A male patient approximately 50 years of age. A dermoscopic close-up of a skin lesion.
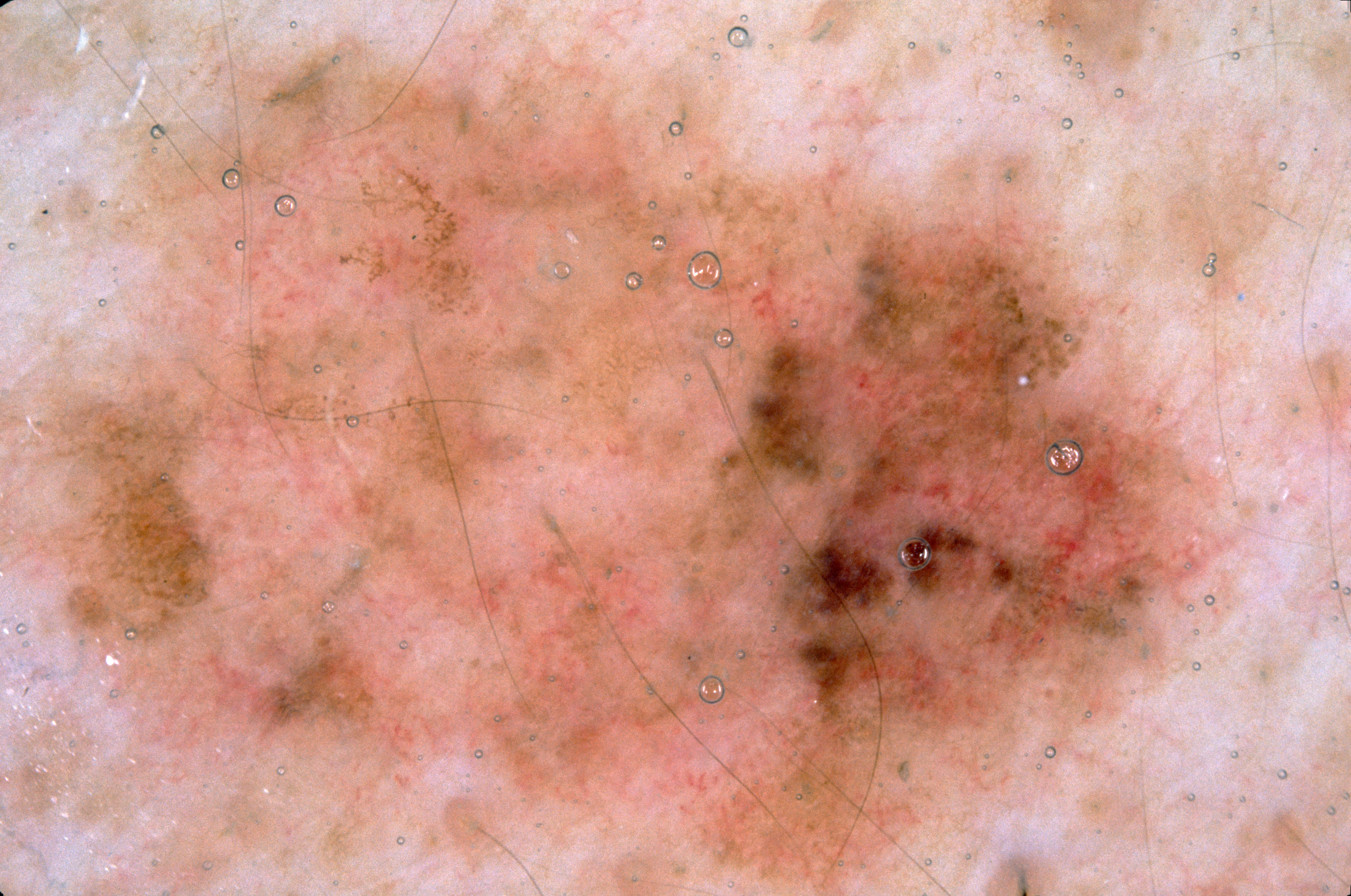Q: Which assessed dermoscopic features were absent?
A: negative network, streaks, milia-like cysts, and pigment network
Q: What is the lesion's bounding box?
A: spans the dermoscopic field
Q: What is the diagnosis?
A: a melanocytic nevus